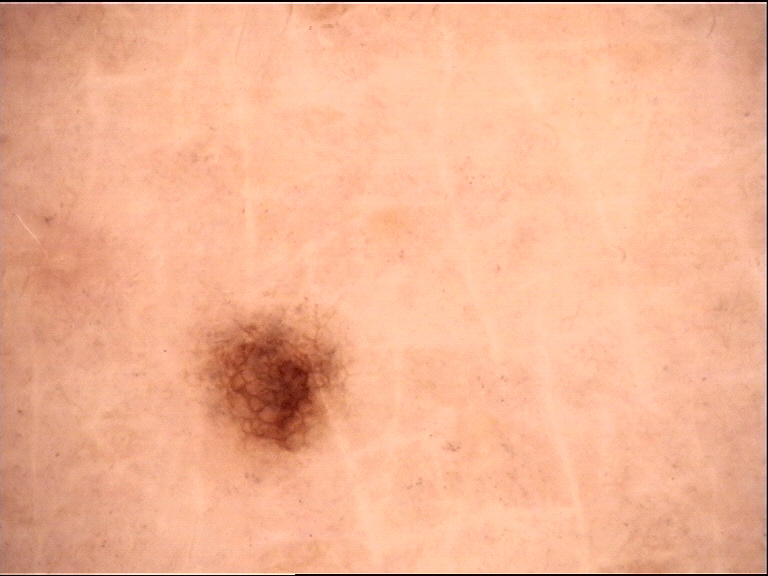Classified as a dysplastic junctional nevus.